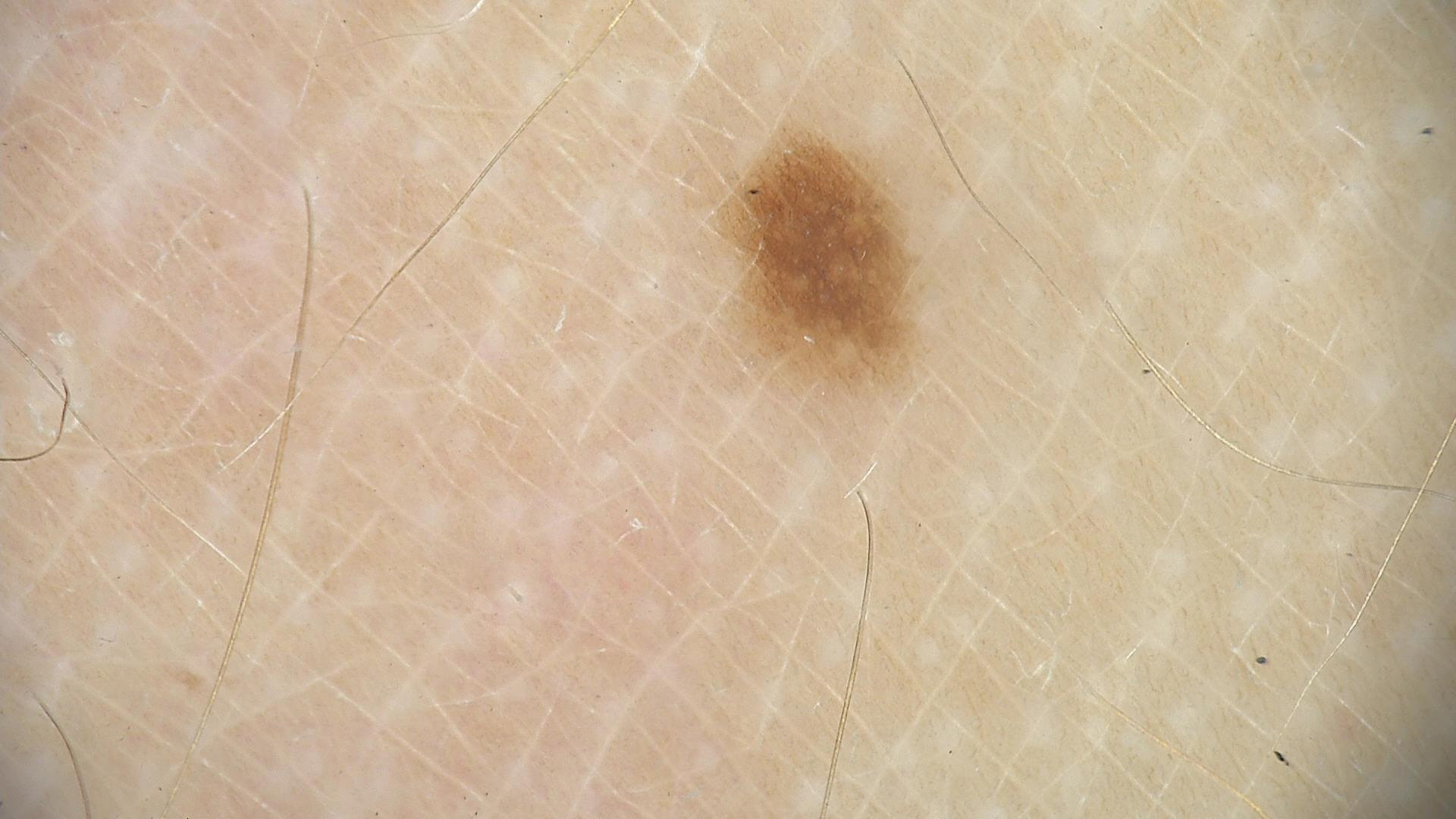- diagnosis · dysplastic junctional nevus (expert consensus)